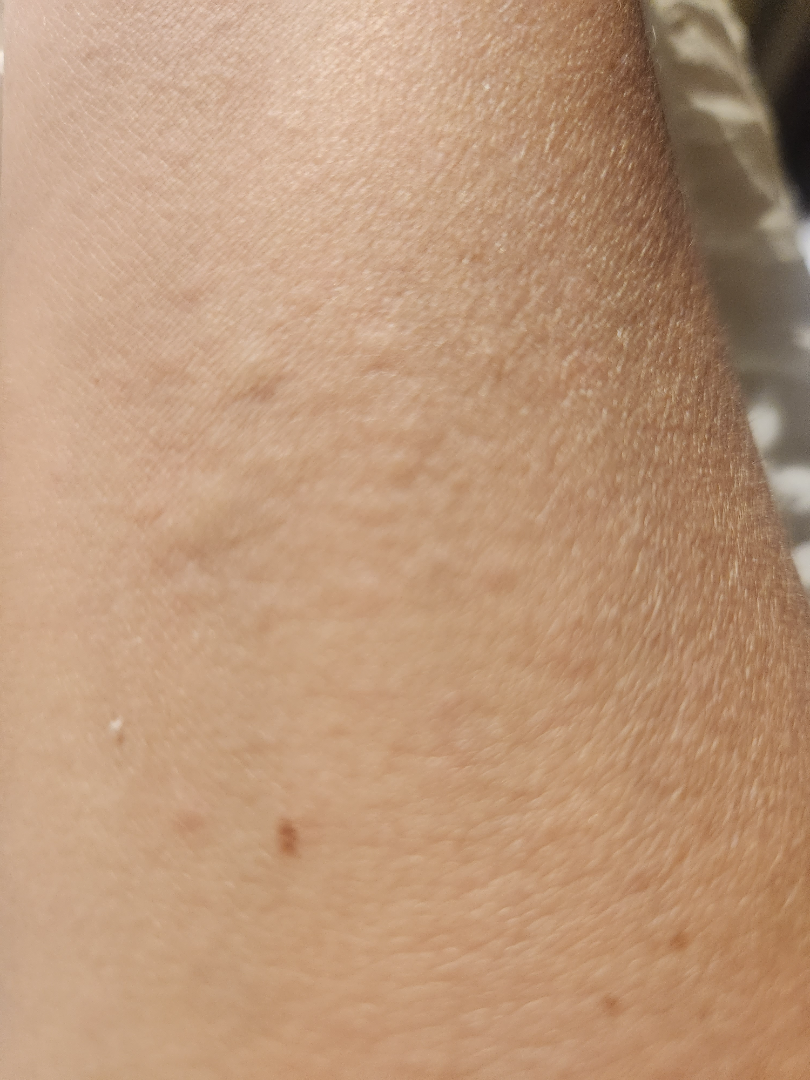History: Located on the leg, back of the torso, front of the torso, palm, head or neck and arm. Close-up view. Impression: Three dermatologists each reviewed the case: favoring Urticaria; less likely is Eczema.